A patient age 32 · a clinical photo of a skin lesion taken with a smartphone — 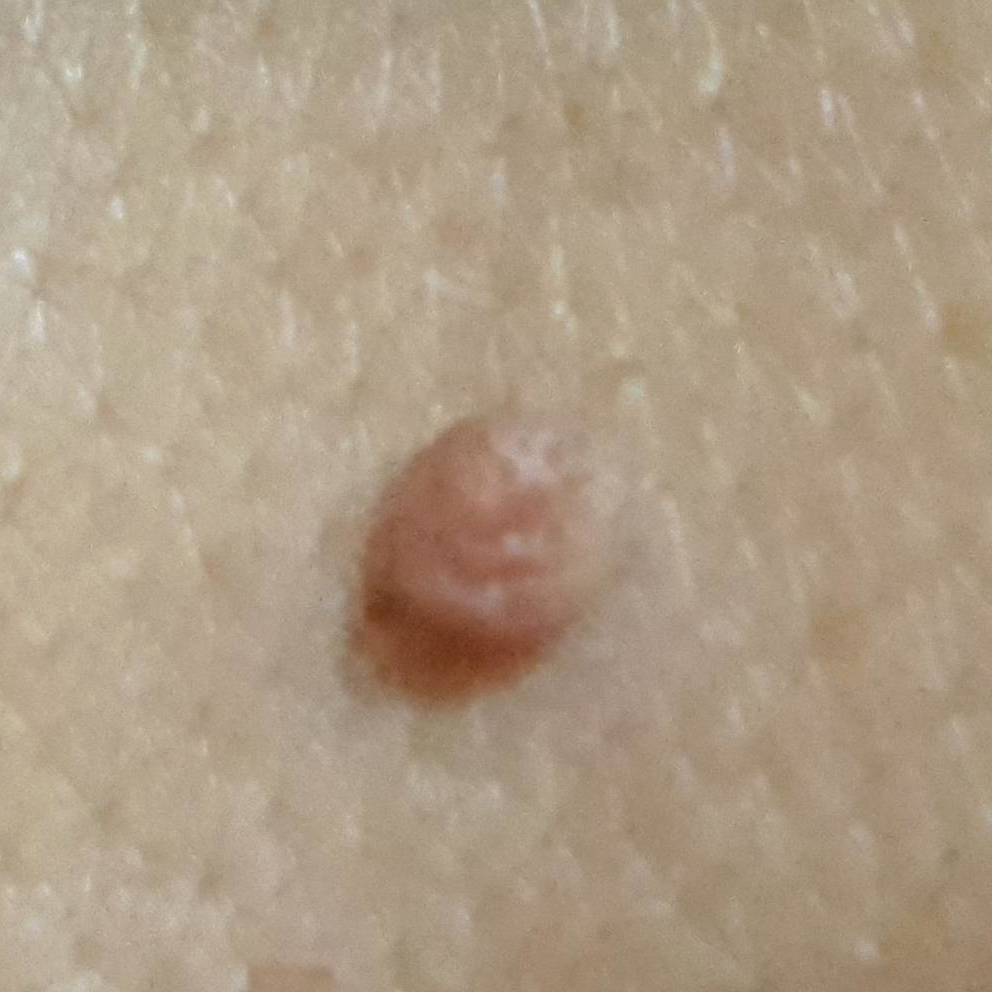body site = the back | symptoms = elevation, growth / no pain | impression = nevus (clinical consensus).